A dermoscopic image of a skin lesion.
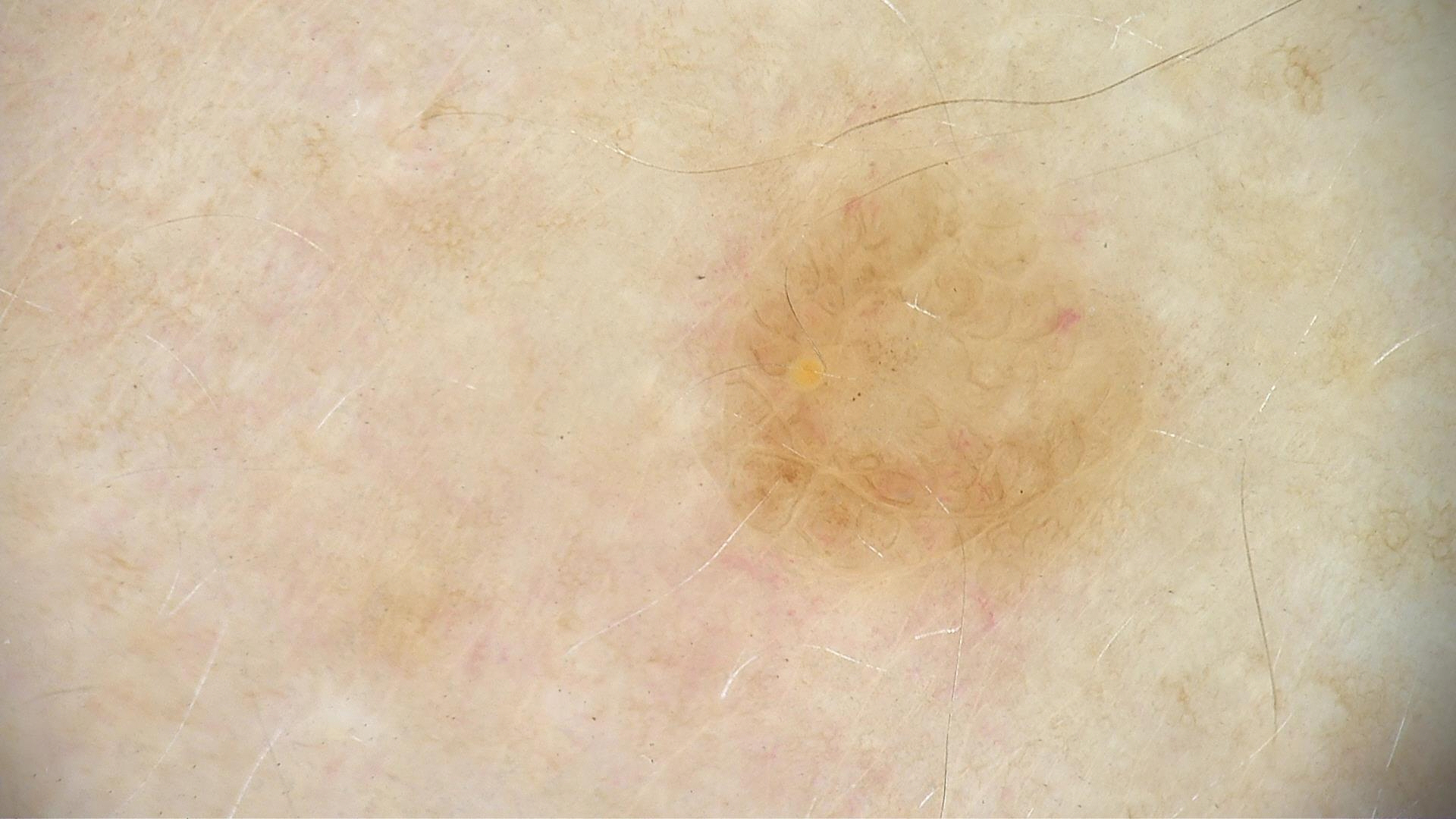Summary: The architecture is that of a banal lesion. Conclusion: Diagnosed as a junctional nevus.